This is a dermoscopic photograph of a skin lesion. A female subject, roughly 70 years of age:
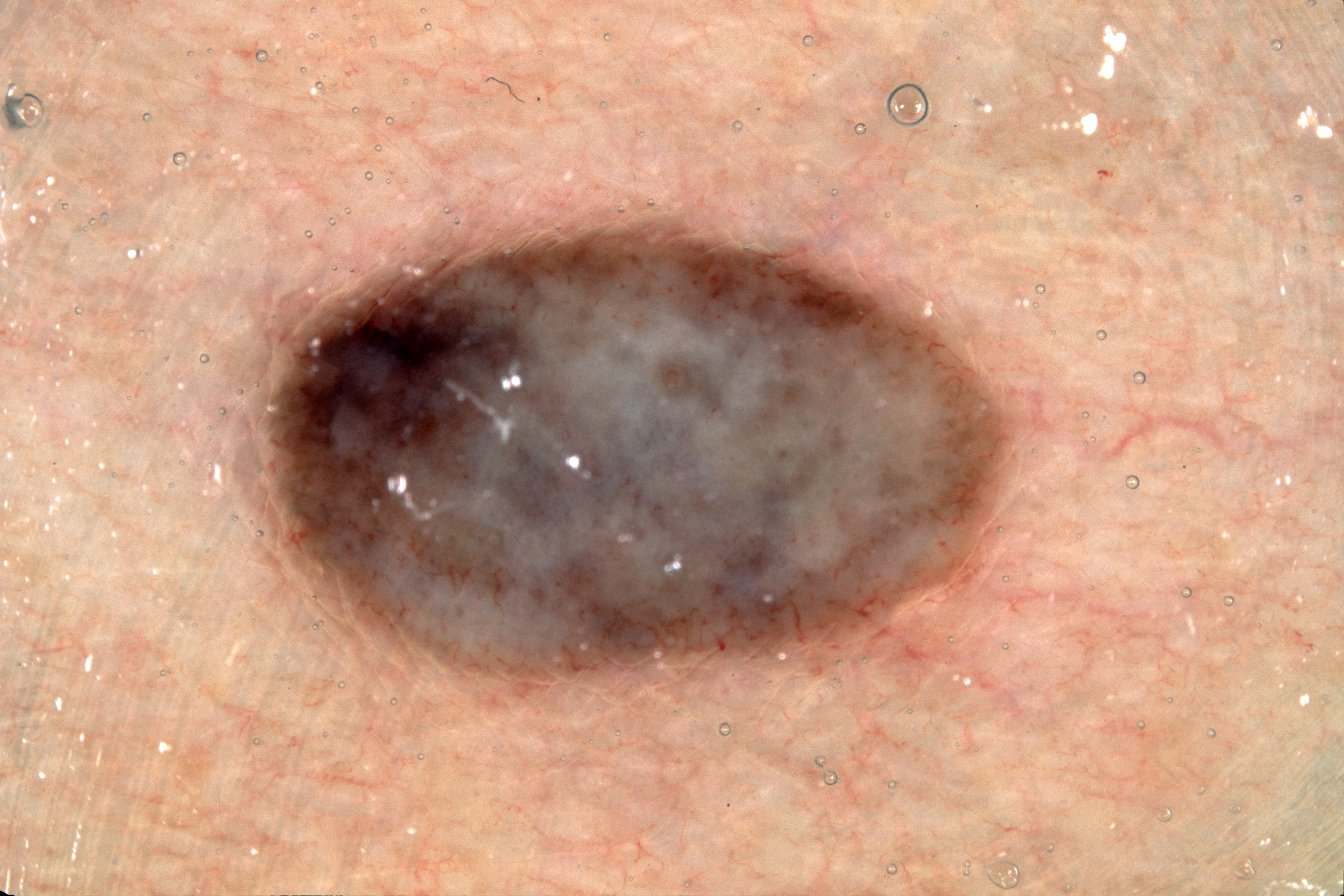Q: Where is the lesion in the image?
A: [262,217,1018,693]
Q: Which assessed dermoscopic features were absent?
A: streaks, pigment network, milia-like cysts, and negative network
Q: What is the diagnosis?
A: a melanocytic nevus, a benign lesion